A dermoscopic photograph of a skin lesion.
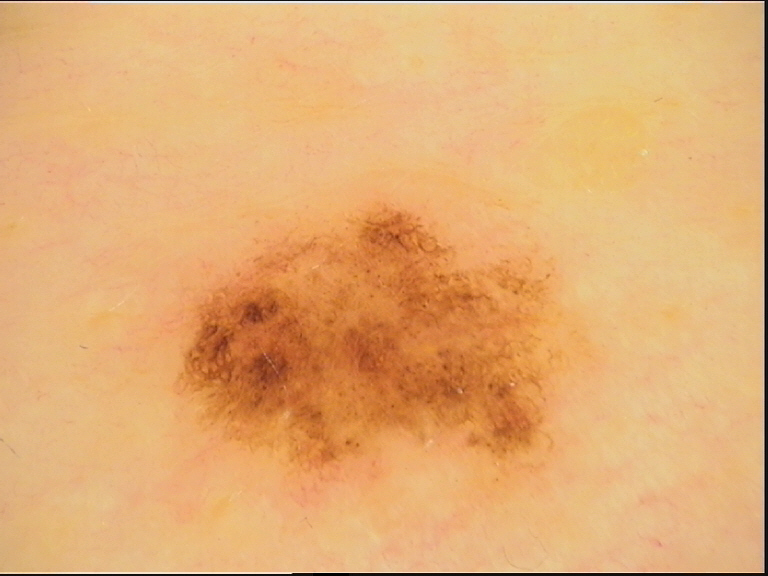<case>
<diagnosis>
<name>dysplastic junctional nevus</name>
<code>jd</code>
<malignancy>benign</malignancy>
<super_class>melanocytic</super_class>
<confirmation>expert consensus</confirmation>
</diagnosis>
</case>